The arm is involved · the photograph was taken at an angle:
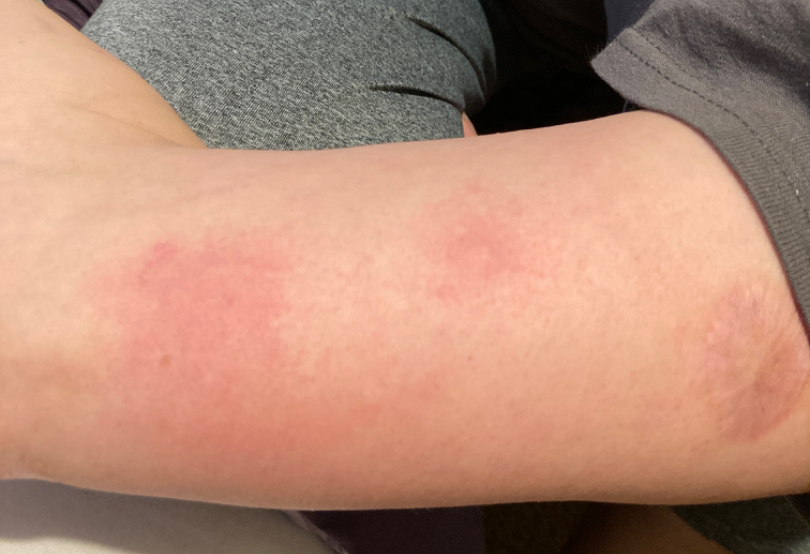The impression on review was Urticaria.